Collected as part of a research study, without a referral diagnosis. Numerous moles by the patient's own estimate. A female patient 26 years old. The patient reports a history of sunbed use. The patient says their skin reddens with sun exposure — 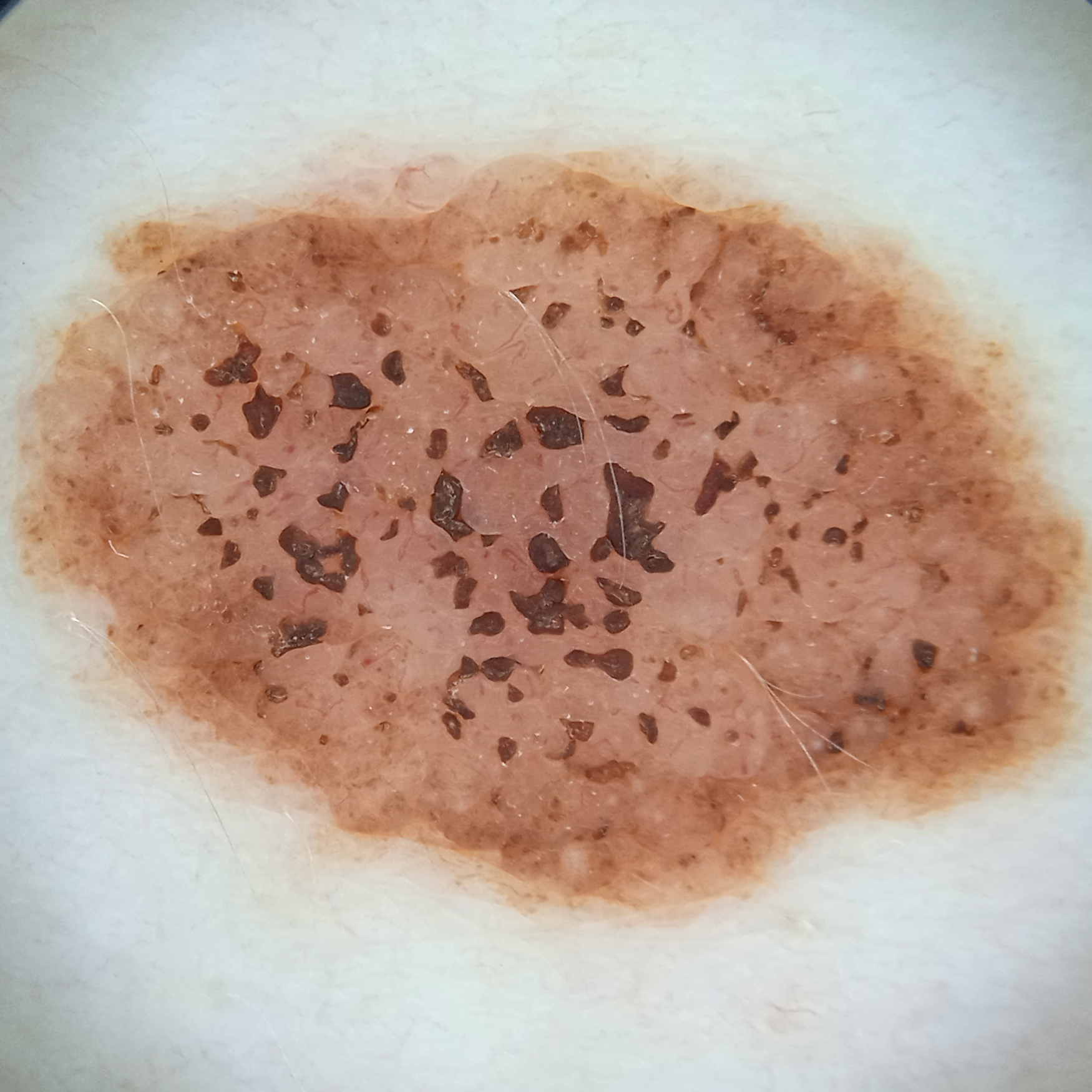Case summary:
Located on the torso. Measuring roughly 12.1 mm.
Impression:
The dermatologists' assessment was a melanocytic nevus.